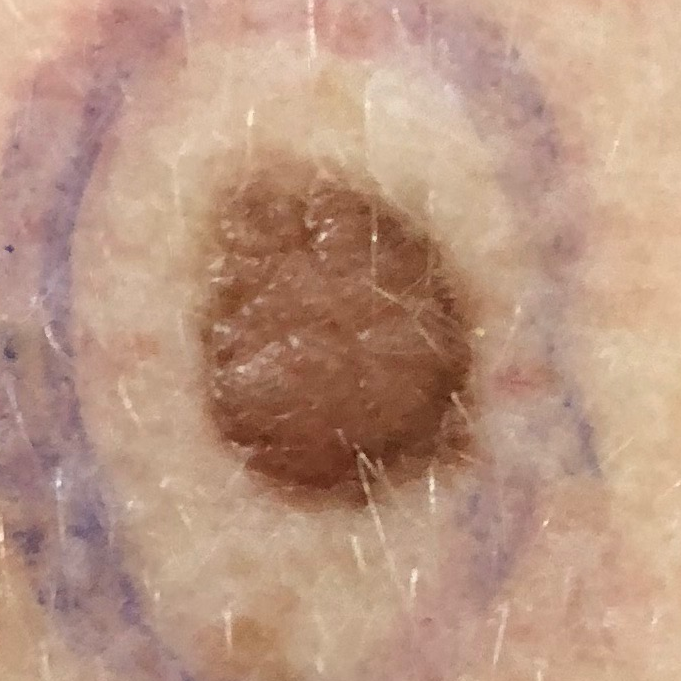Biopsy-confirmed as a nevus.